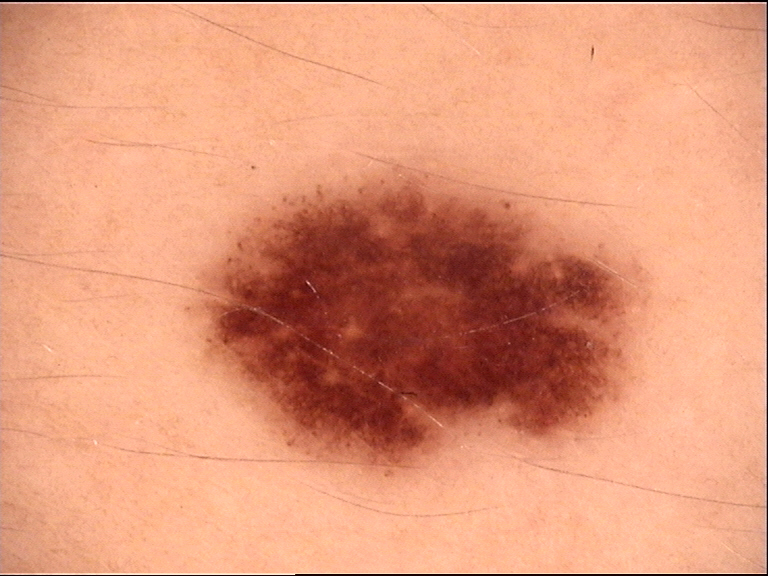Impression: Consistent with a dysplastic junctional nevus.